Located on the leg and arm · an image taken at a distance · the patient is a female aged 18–29.
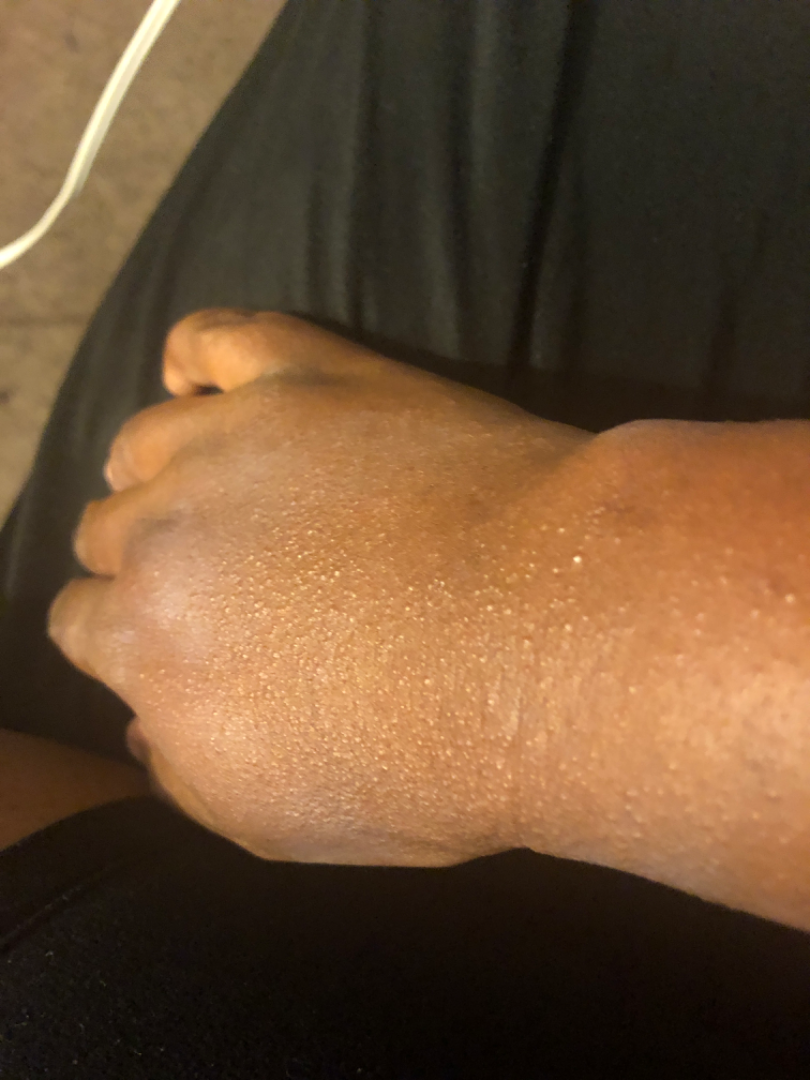| field | value |
|---|---|
| assessment | the differential is split between Miliaria and Contact dermatitis, NOS; a remote consideration is Drug Rash |